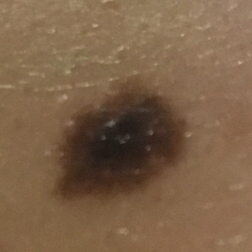| feature | finding |
|---|---|
| modality | clinical photograph |
| risk factors | prior malignancy (patient or family), no alcohol use, no tobacco use |
| subject | female, in their 30s |
| Fitzpatrick | II |
| location | the back |
| size | 7x6 mm |
| symptoms | no pain |
| diagnosis | nevus (biopsy-proven) |